A male patient, aged approximately 50 · a skin lesion imaged with a dermatoscope.
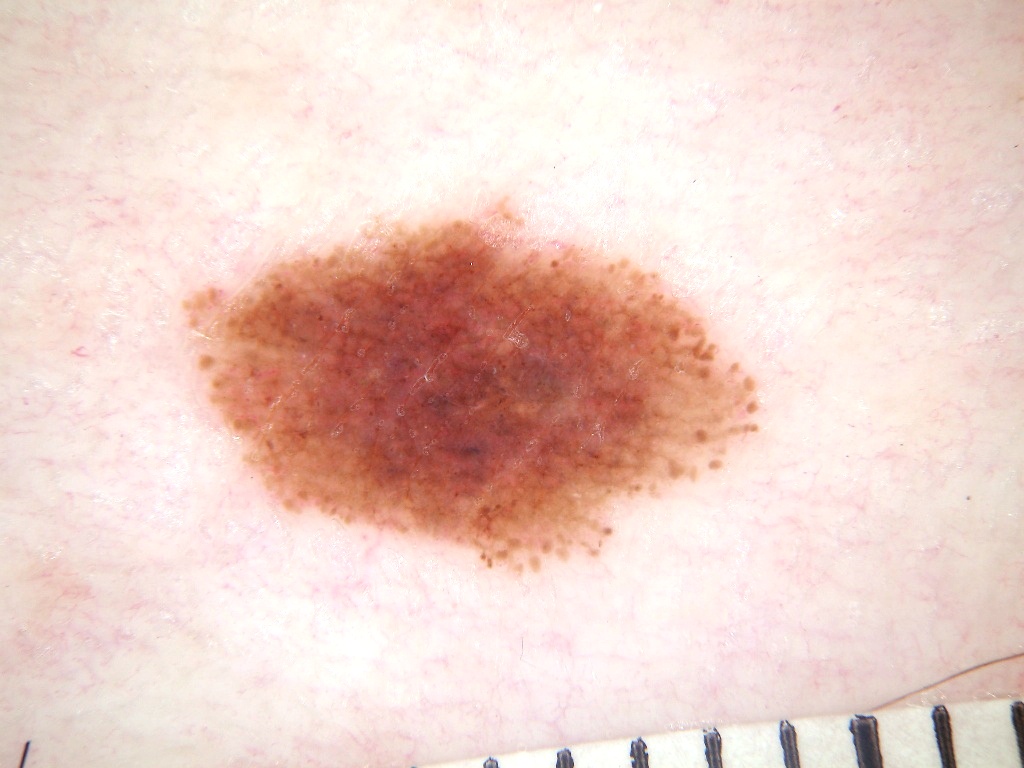Case summary: Dermoscopic review identifies pigment network and globules. With coordinates (x1, y1, x2, y2), the lesion is bounded by <bbox>178, 199, 758, 573</bbox>. Impression: Expert review diagnosed this as a melanocytic nevus.